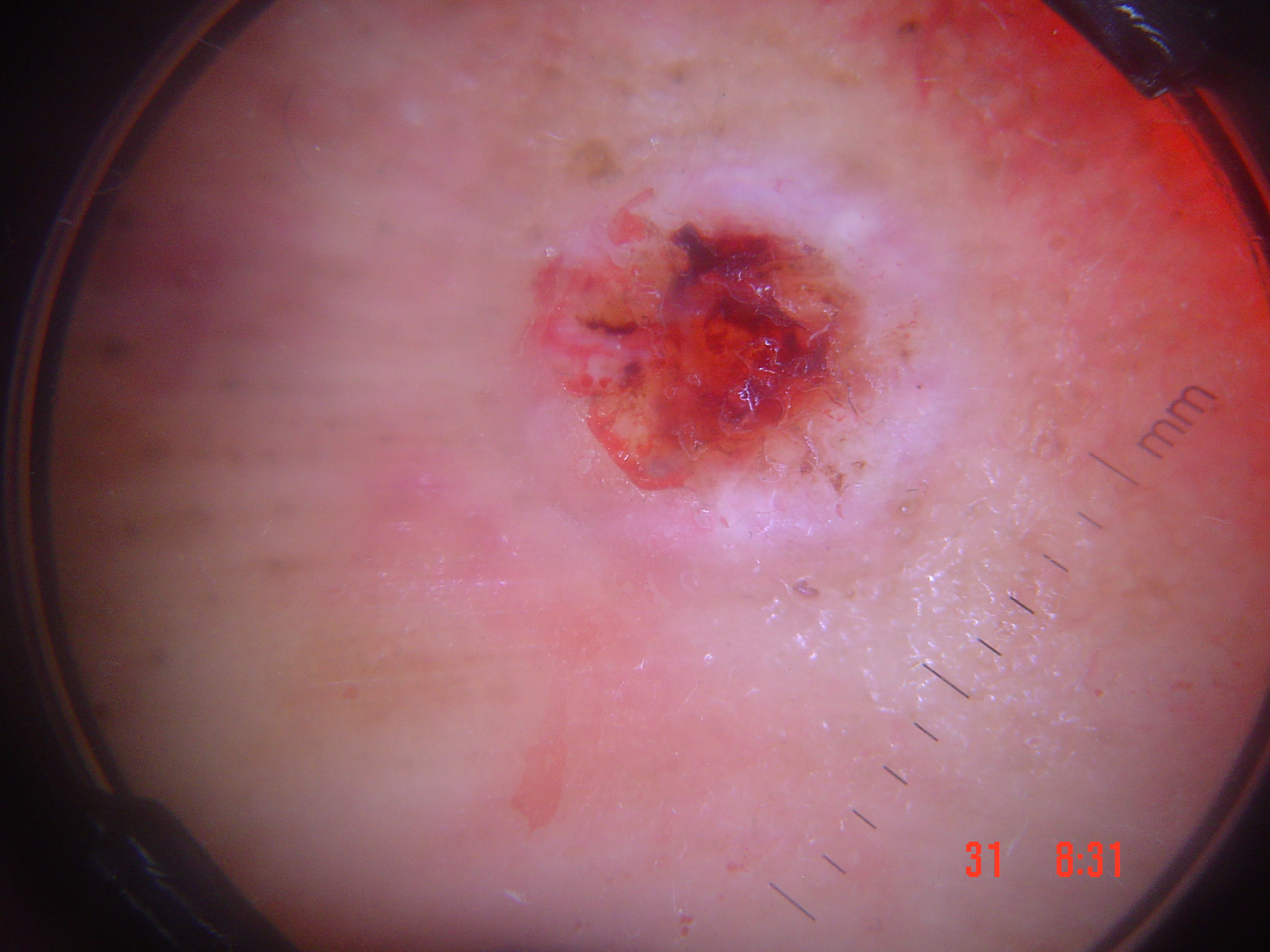{"image": "dermatoscopy", "lesion_type": {"main_class": "keratinocytic"}, "diagnosis": {"name": "squamous cell carcinoma", "code": "scc", "malignancy": "malignant", "super_class": "non-melanocytic", "confirmation": "histopathology"}}